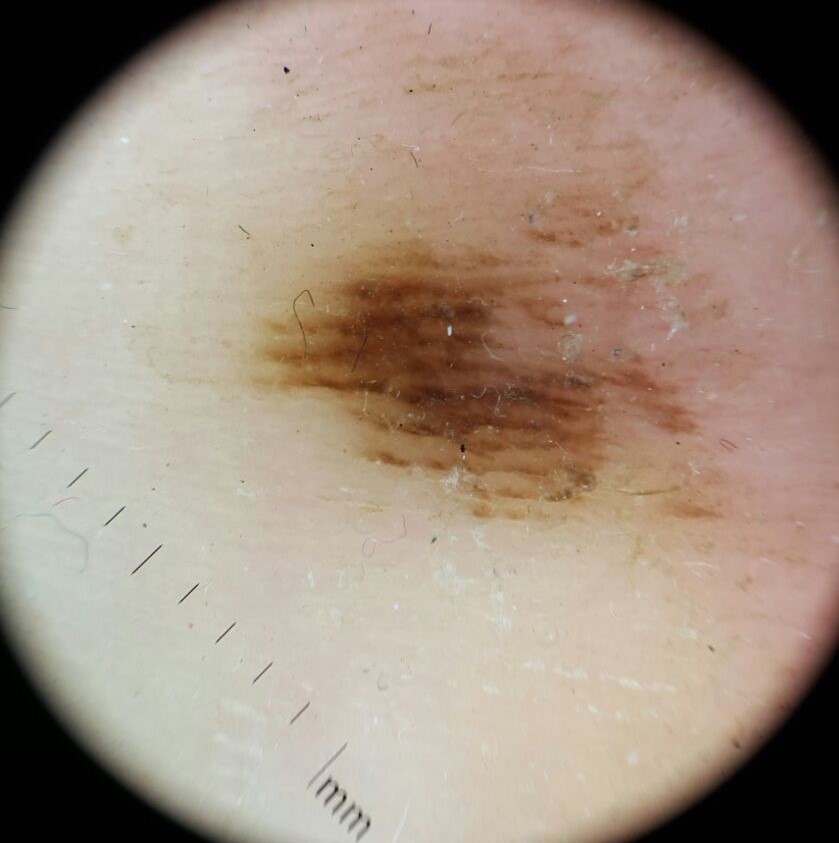Dermoscopy of a skin lesion.
Diagnosed as a benign lesion — an acral dysplastic junctional nevus.